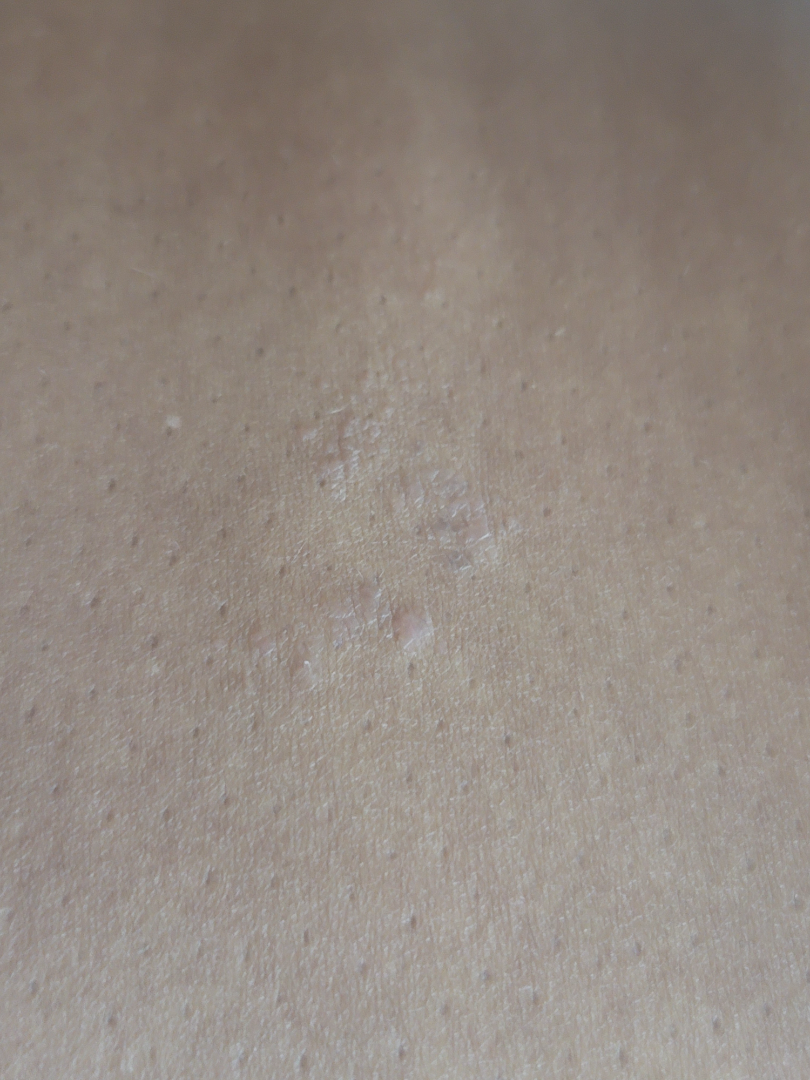symptoms = bothersome appearance and enlargement; subject = female, age 40–49; described texture = raised or bumpy; affected area = leg; history = one to four weeks; constitutional symptoms = joint pain; shot type = close-up; clinical impression = favoring Eczema.